Fitzpatrick skin type III; non-clinician graders estimated MST 2 or 3 · this is a close-up image:
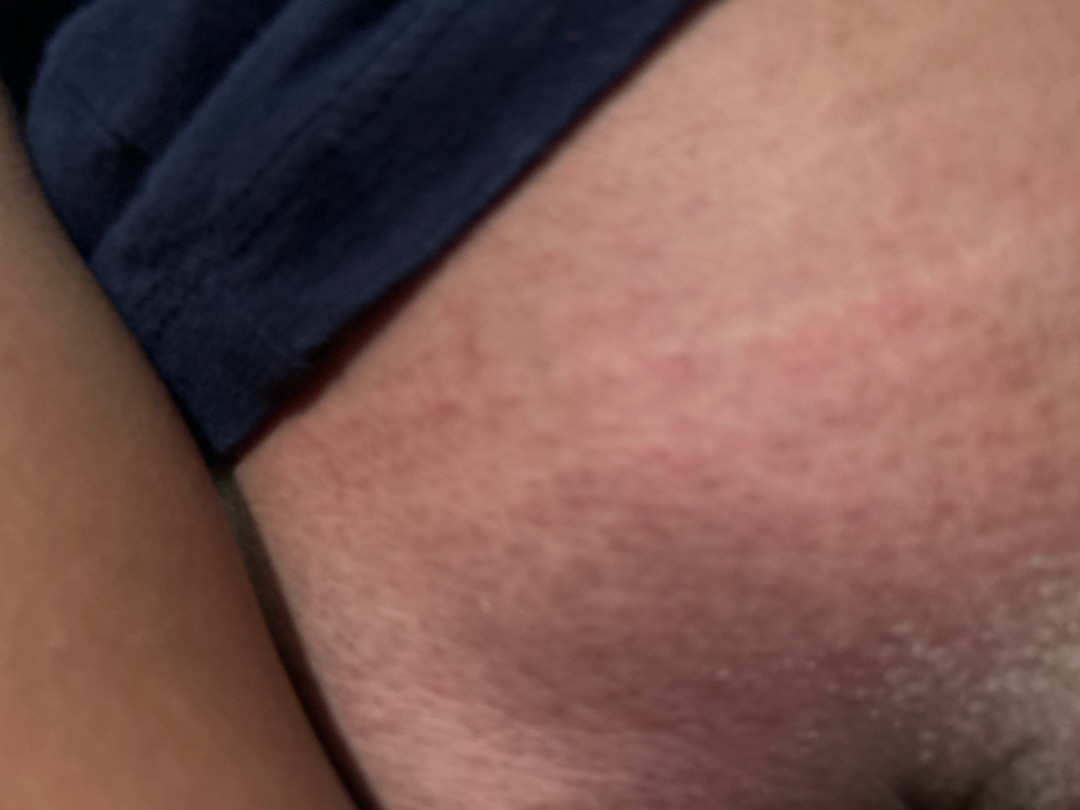Review:
Single-reviewer assessment: the differential is split between Keratosis pilaris and Eczema.